A dermatoscopic image of a skin lesion.
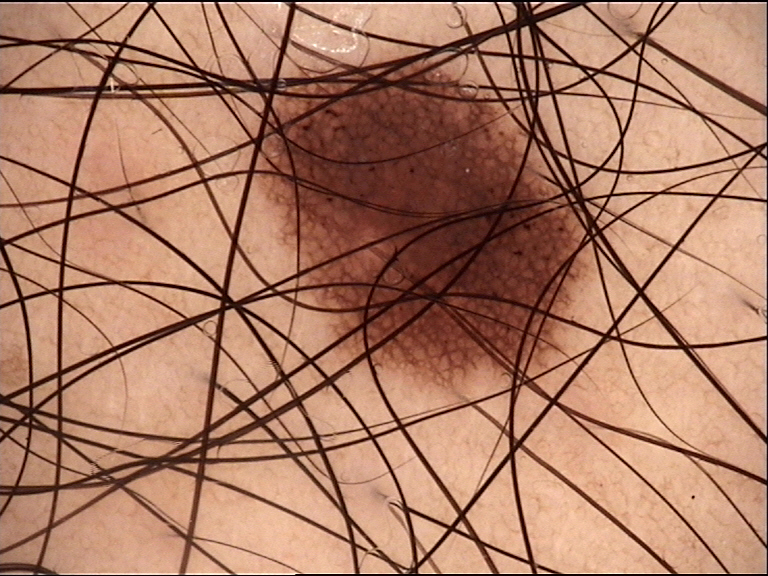The architecture is that of a banal lesion. The diagnostic label was a junctional nevus.